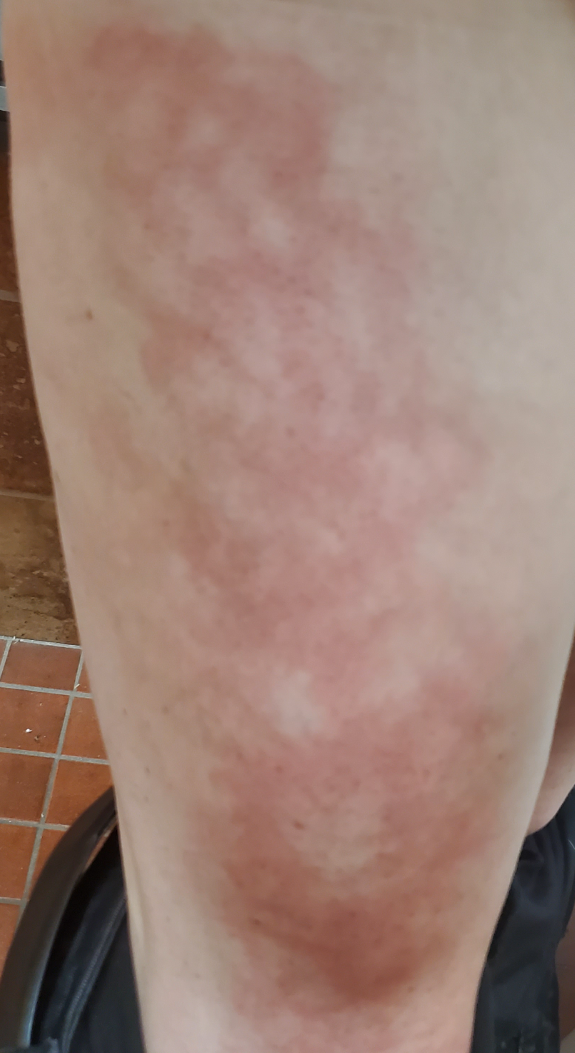| field | value |
|---|---|
| body site | leg |
| view | close-up |
| texture | flat |
| systemic symptoms | chills, joint pain, fever, shortness of breath and fatigue |
| duration | about one day |
| dermatologist impression | consistent with Erythema ab igne |